The photograph was taken at a distance — 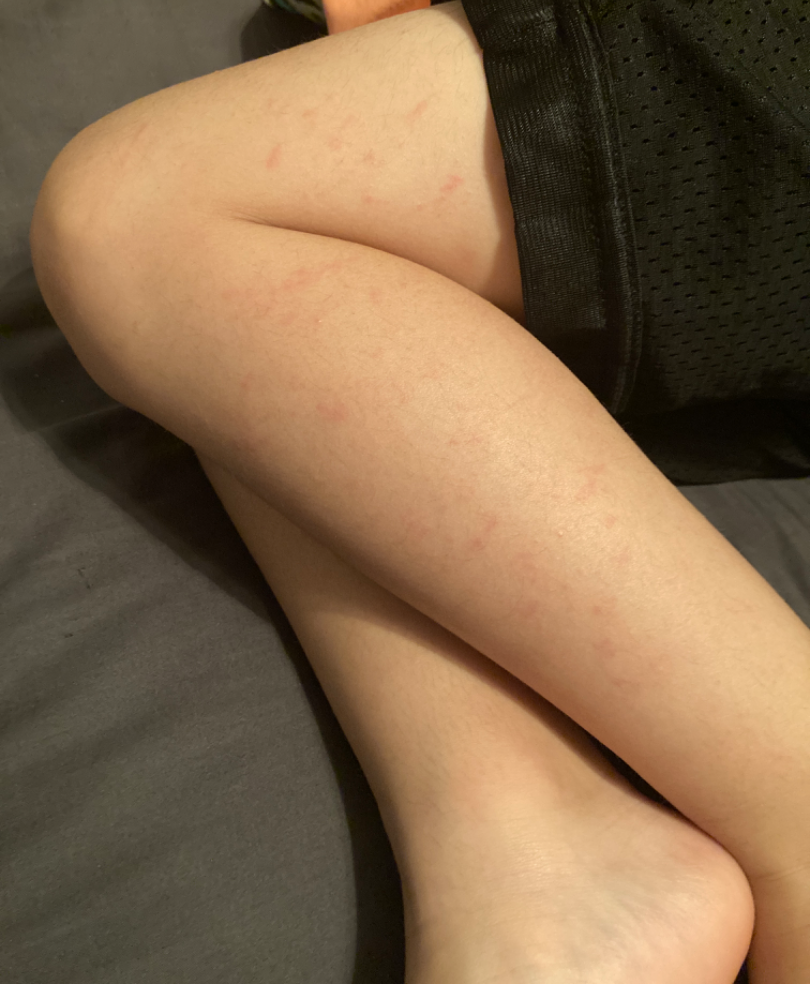Q: Could the case be diagnosed?
A: unable to determine